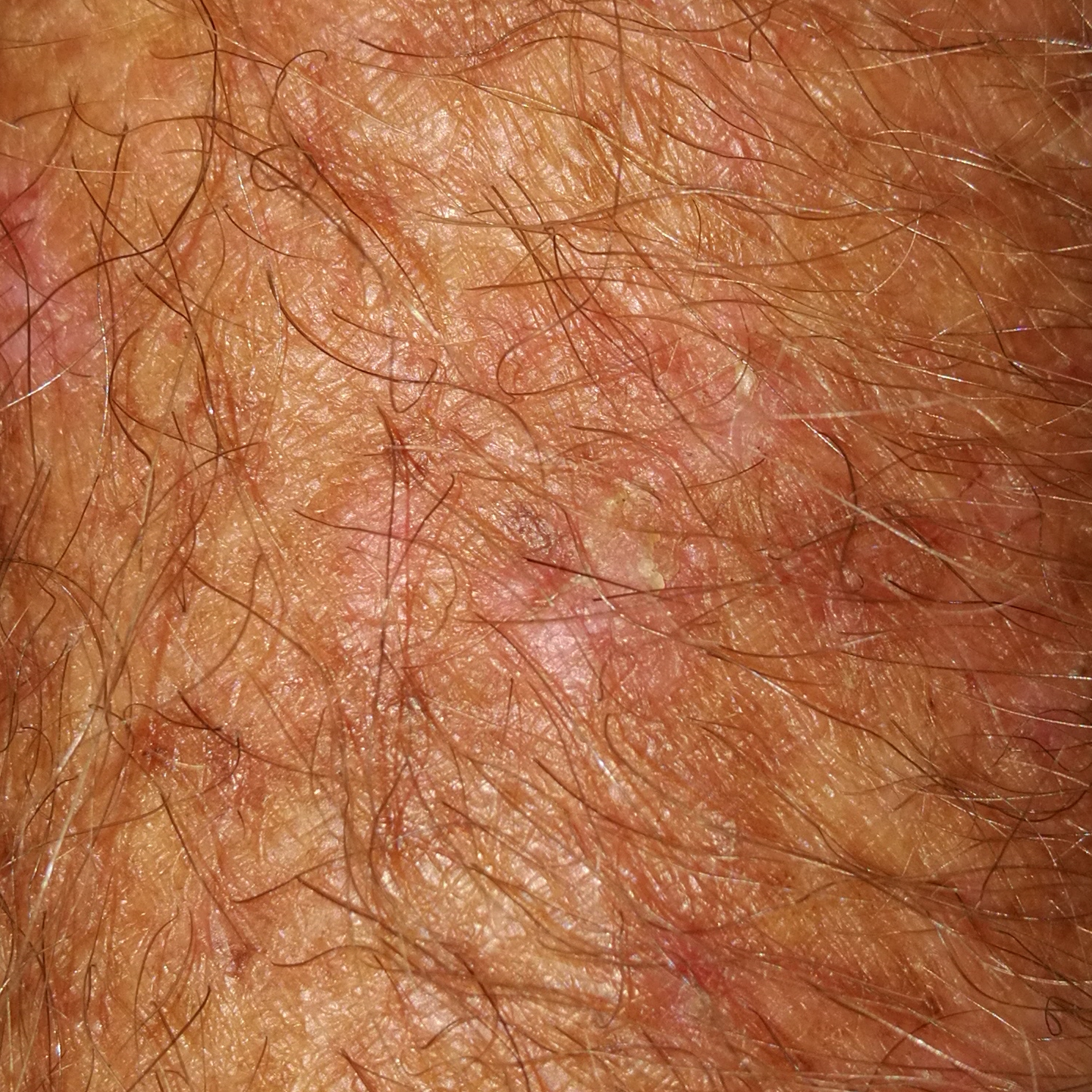Clinical context:
A clinical close-up photograph of a skin lesion. A subject 68 years of age. The lesion is on a forearm. The patient reports that the lesion itches, but has not bled and has not grown.
Impression:
Expert review favored a lesion of indeterminate malignant potential — an actinic keratosis.